A dermoscopic image of a skin lesion:
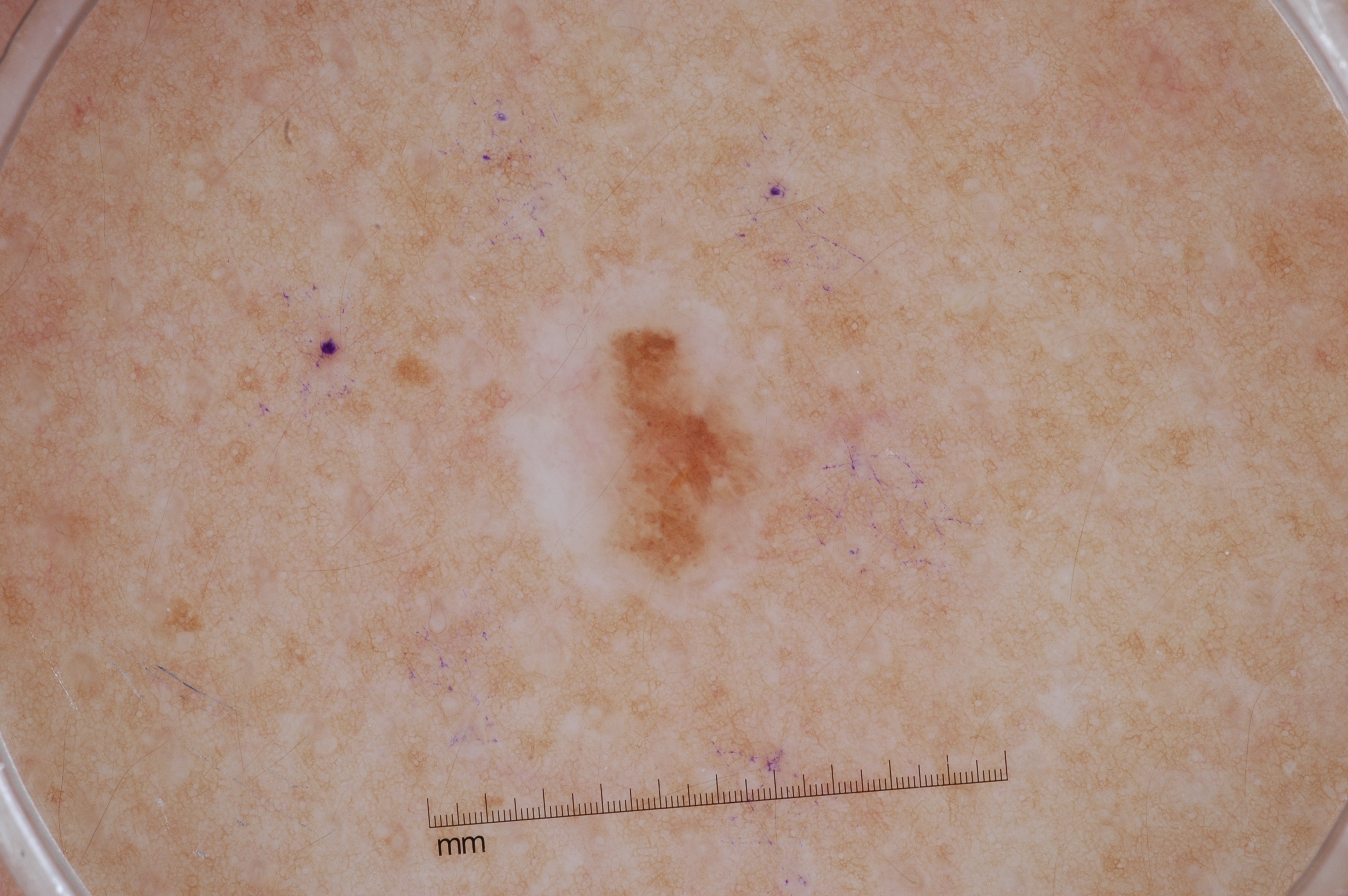On dermoscopy, the lesion shows no milia-like cysts, streaks, negative network, or pigment network. With coordinates (x1, y1, x2, y2), the lesion is bounded by 478/230/808/627. Consistent with a melanocytic nevus.